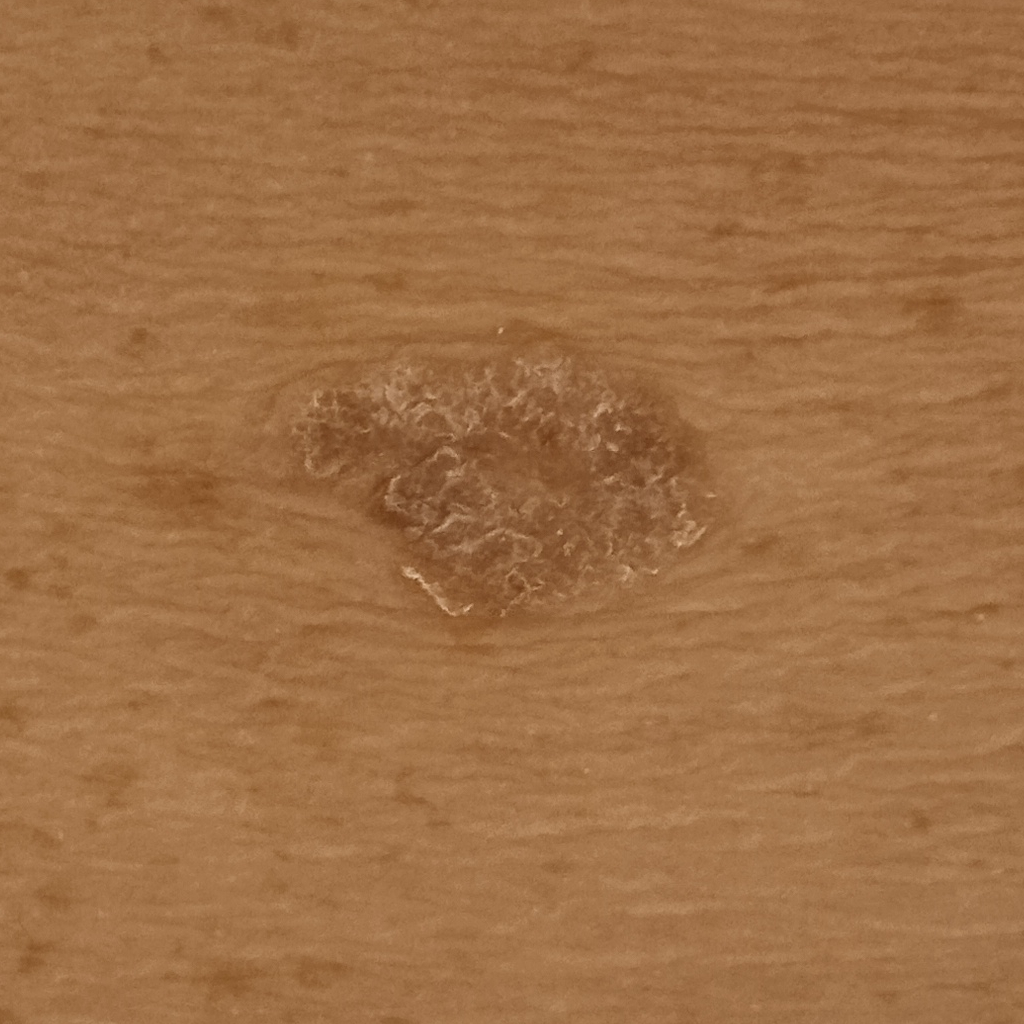The patient describes having few moles overall.
By self-report, a personal history of cancer.
A male subject aged 72.
The lesion is on the back.
Measuring roughly 16.5 mm.
The consensus diagnosis for this lesion was a seborrheic keratosis.